A dermatoscopic image of a skin lesion:
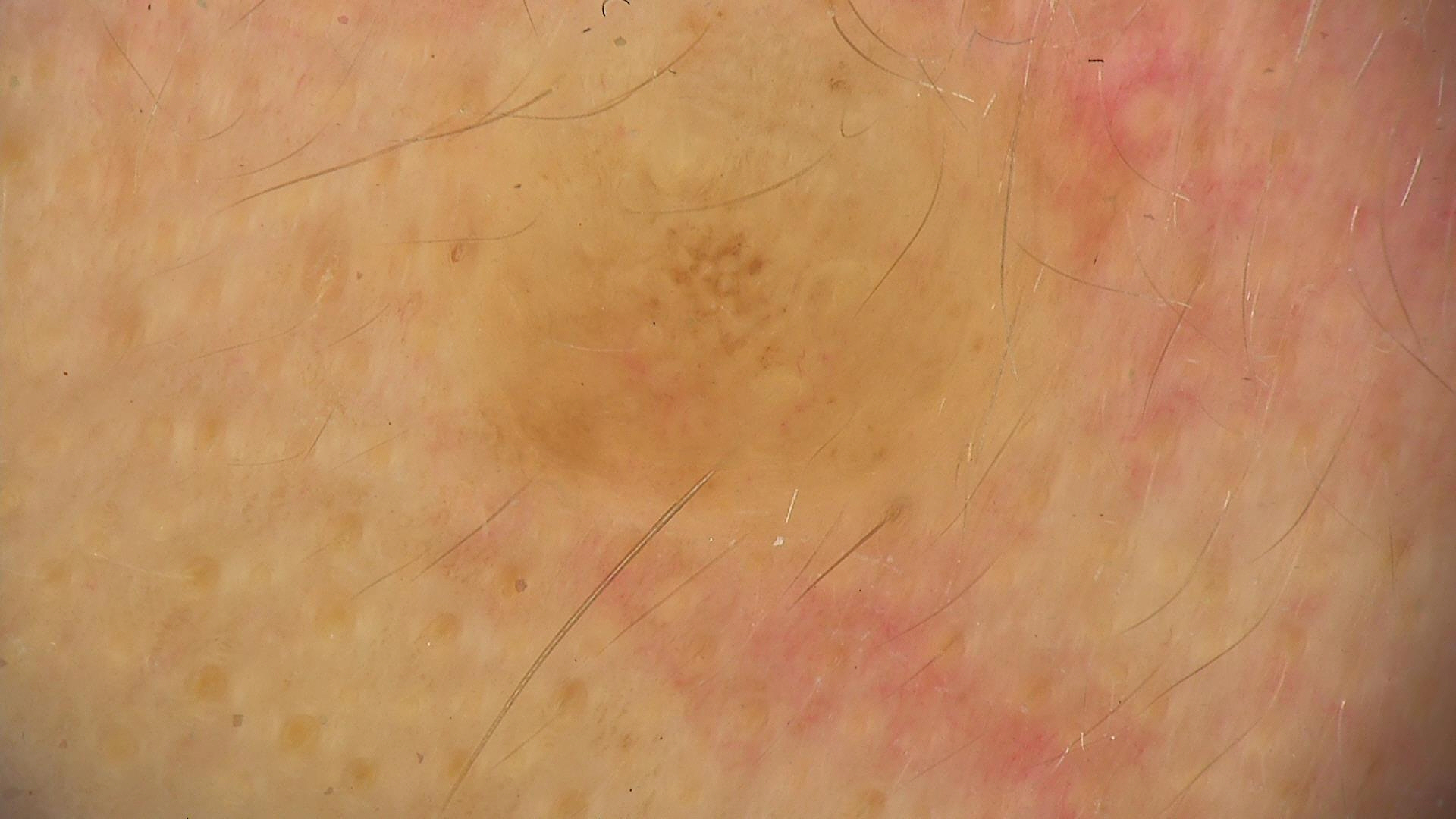Q: What is this lesion?
A: dermal nevus (expert consensus)